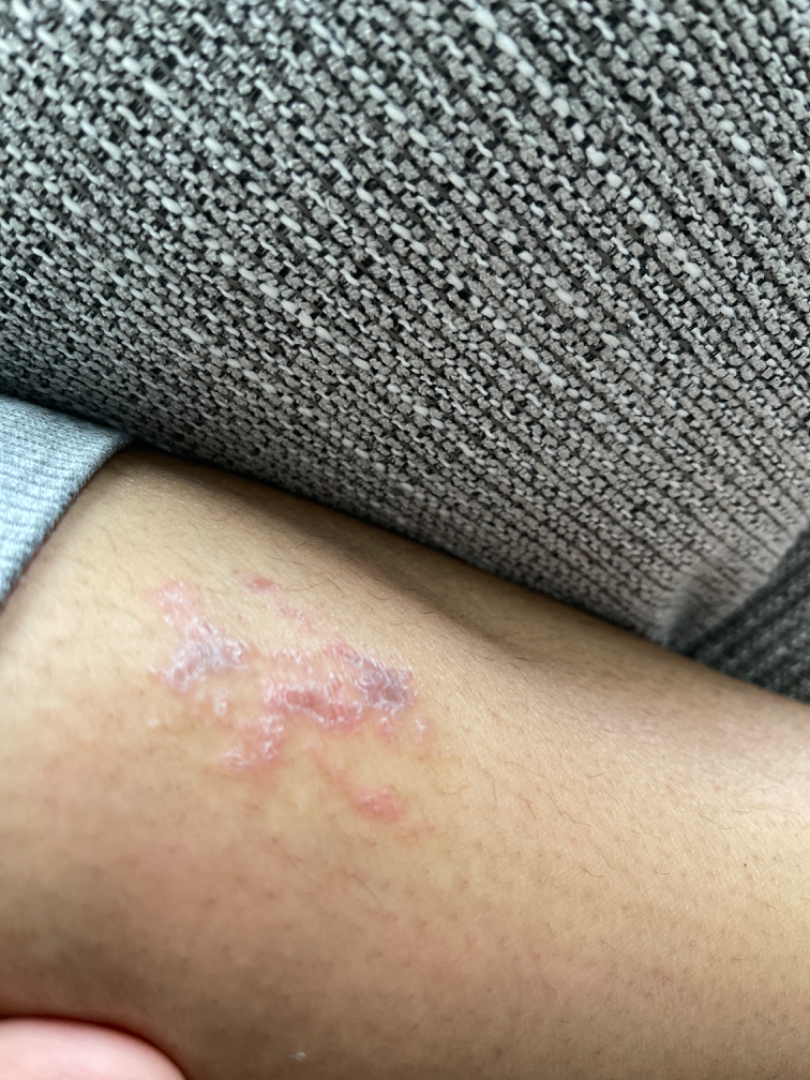Reviewed remotely by three dermatologists: favoring Eczema; less probable is Tinea; a more distant consideration is Cutaneous larva migrans; less likely is Lichen planus/lichenoid eruption; lower on the differential is Allergic Contact Dermatitis.